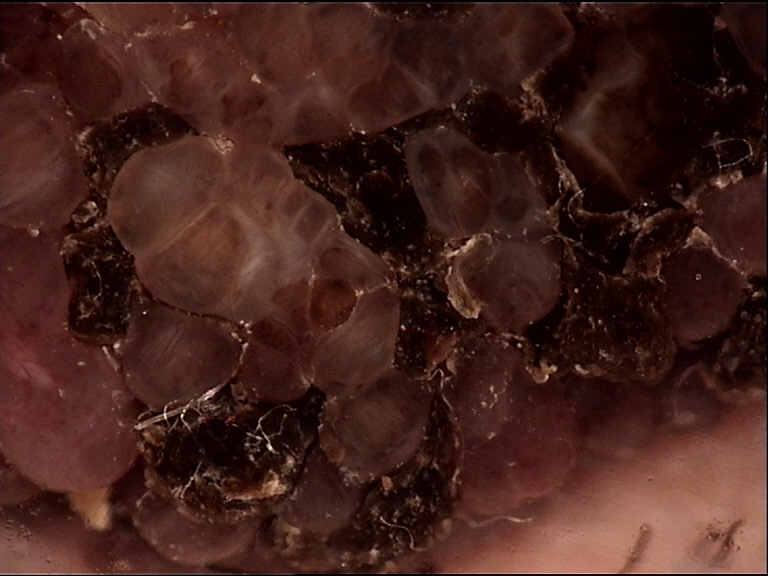A dermoscopic image of a skin lesion. Classified as a banal lesion — a congenital compound nevus.